Collected as part of a research study, without a referral diagnosis. The patient says their skin tans without first burning. A female subject age 68. The patient describes having few moles overall. A macroscopic clinical photograph of a skin lesion — 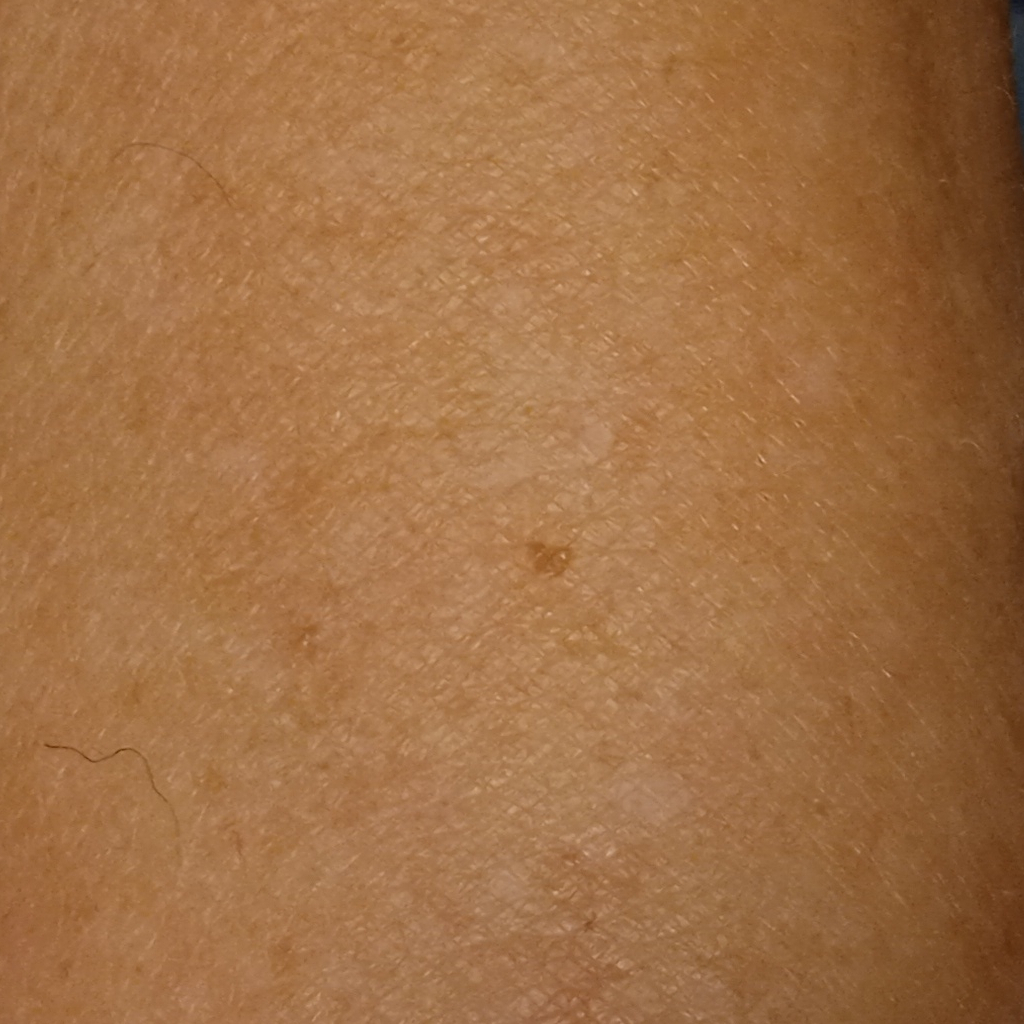The lesion involves an arm. The lesion is about 1.7 mm across. The diagnostic impression was a melanocytic nevus.